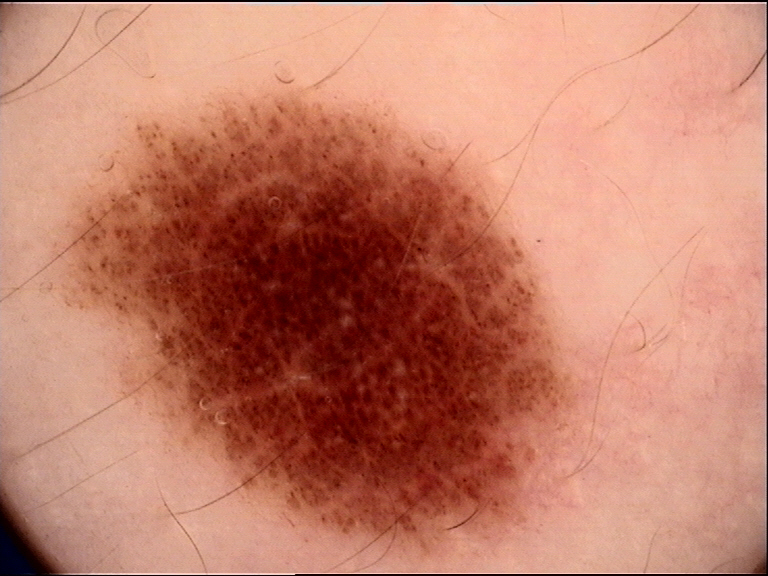The diagnosis was a dysplastic compound nevus.